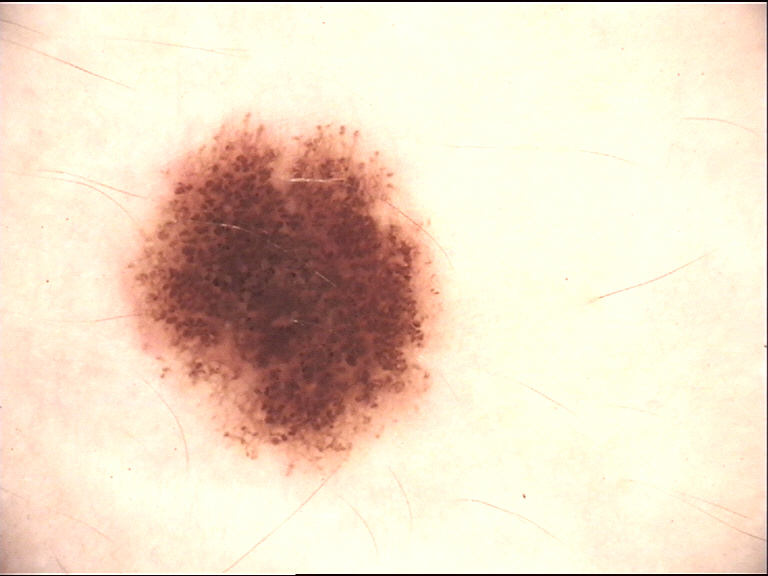| key | value |
|---|---|
| diagnosis | compound nevus (expert consensus) |